Self-categorized by the patient as a rash · the patient notes the condition has been present for one to four weeks · the subject is 30–39, female · the patient notes the lesion is rough or flaky and raised or bumpy · this image was taken at a distance · the lesion involves the top or side of the foot and leg:
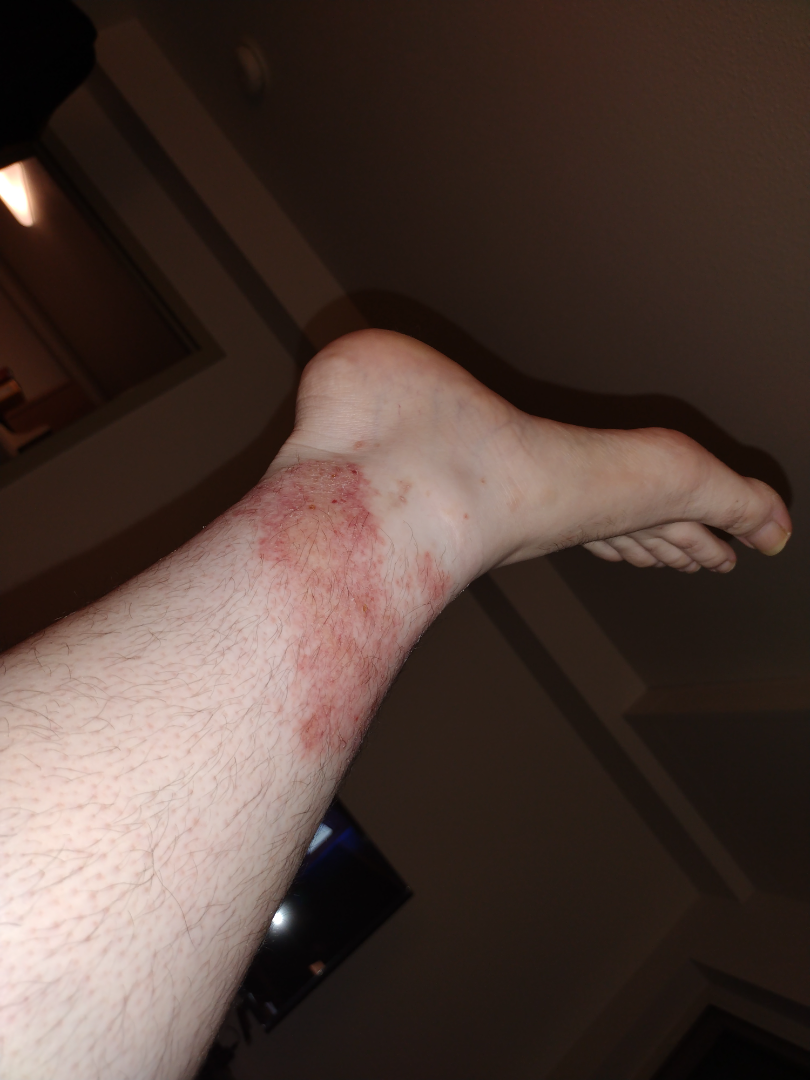clinical impression = three dermatologists independently reviewed the case: Allergic Contact Dermatitis and Stasis Dermatitis were each considered, in no particular order; also on the differential is Eczema; a remote consideration is Irritant Contact Dermatitis; less likely is Contact dermatitis